The subject is a male in their mid-60s; this is a dermoscopic photograph of a skin lesion.
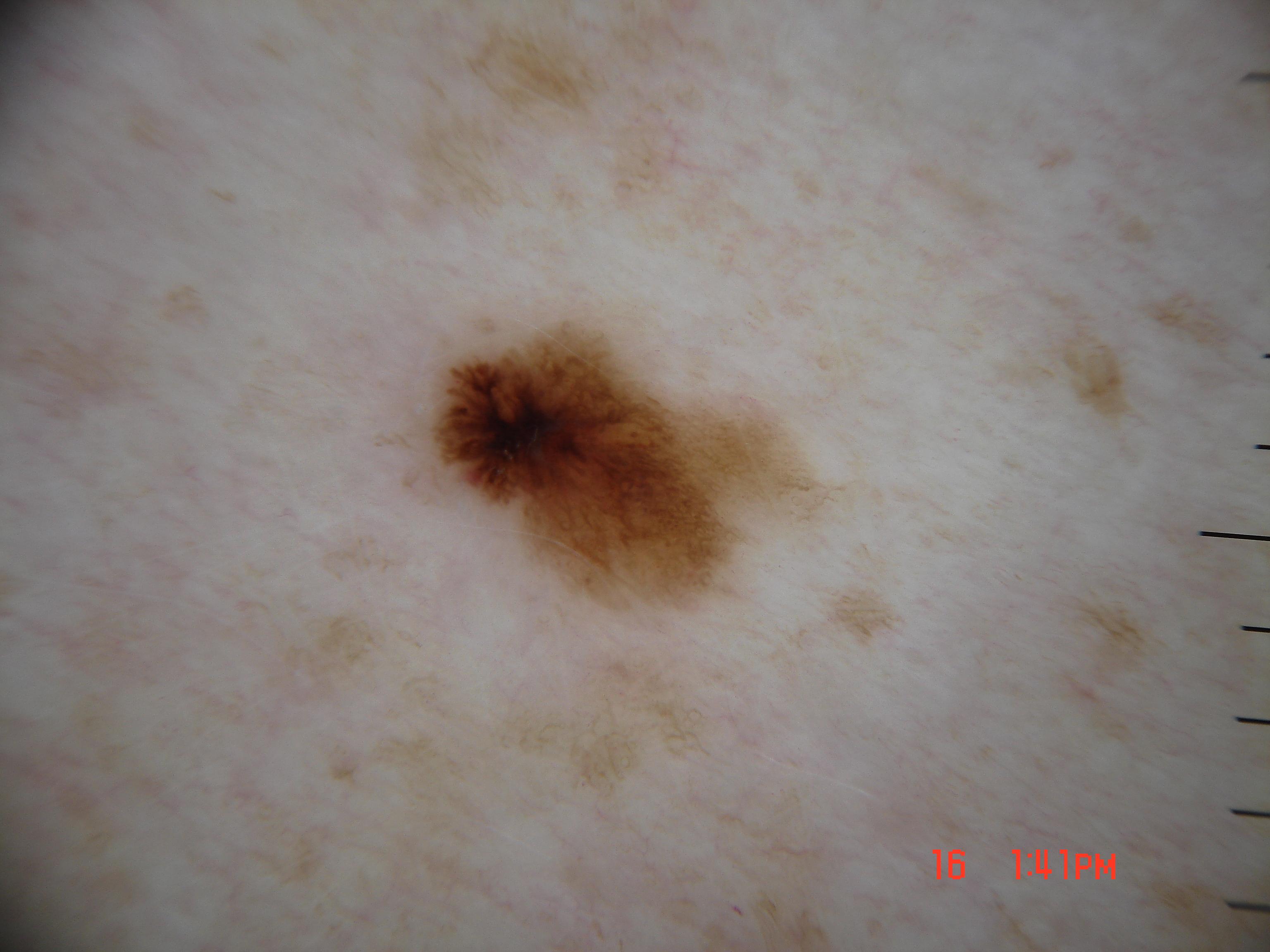Image and clinical context: The lesion covers approximately 8% of the dermoscopic field. In (x1, y1, x2, y2) order, the lesion is located at <box>428, 304, 873, 642</box>. Dermoscopic review identifies pigment network, streaks, and globules; no milia-like cysts or negative network. Diagnosis: Histopathologically confirmed as a melanoma, a skin cancer.